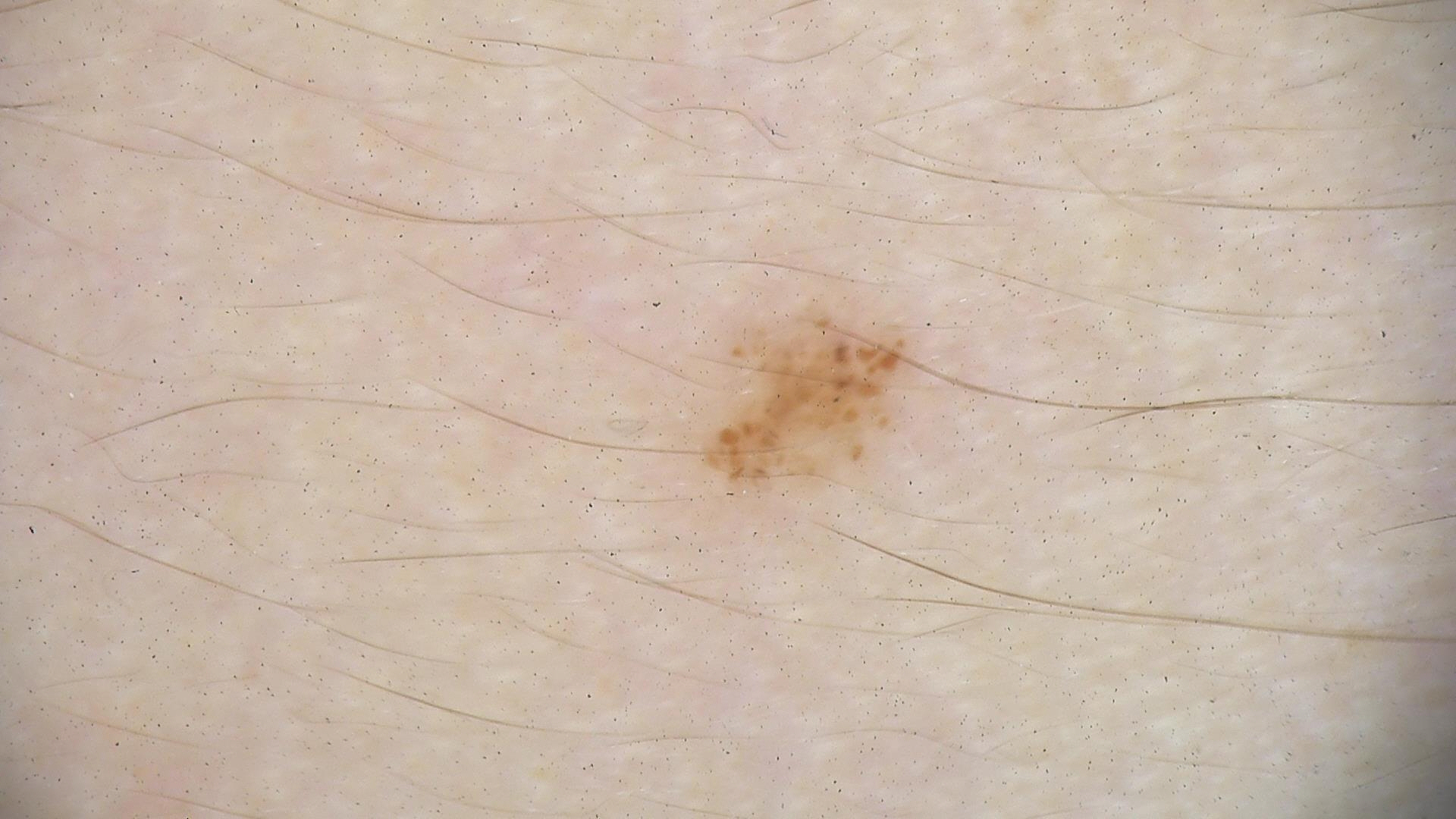Classified as a dysplastic junctional nevus.